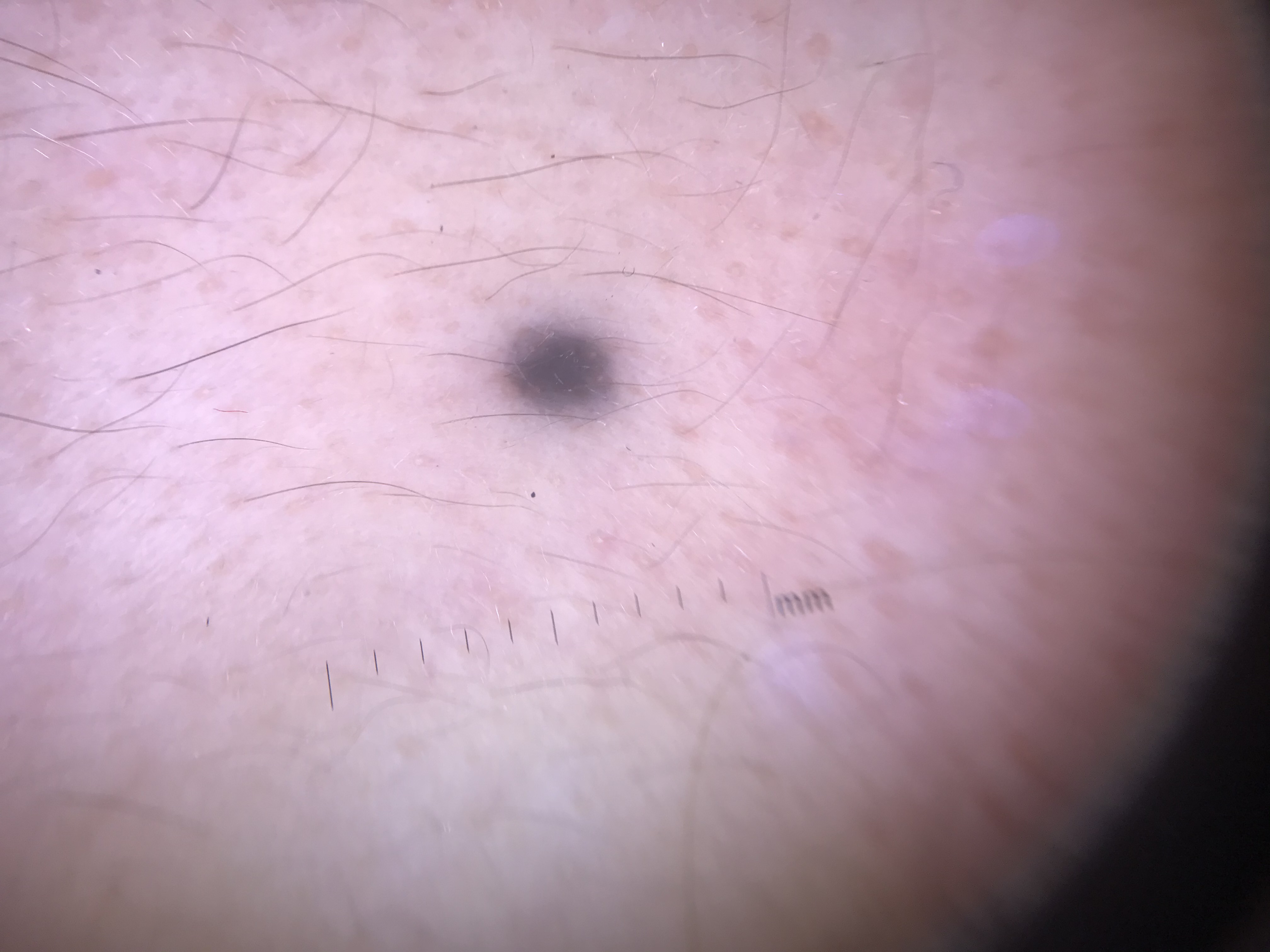image=dermatoscopy
diagnosis=blue nevus (expert consensus)